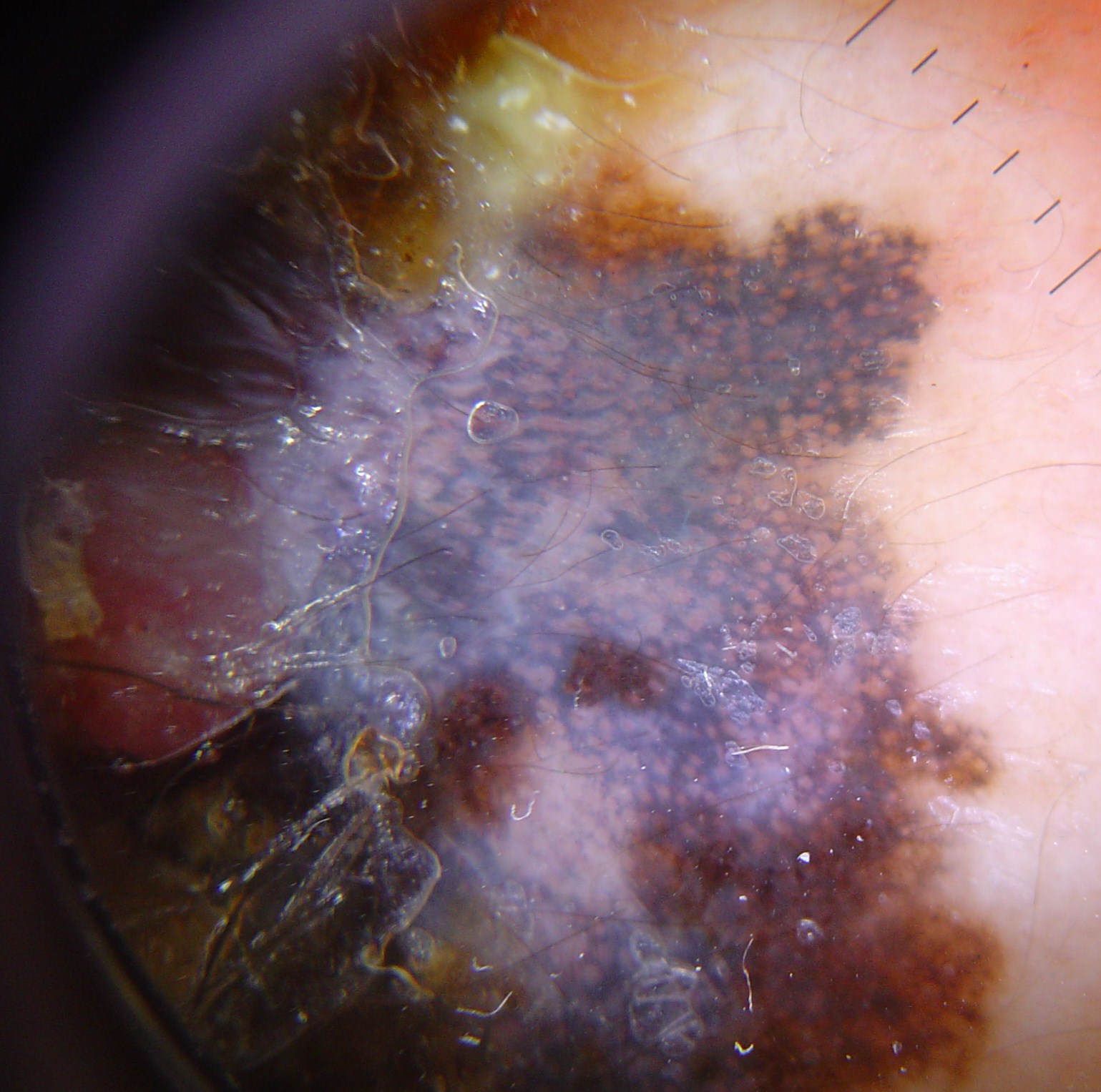Dermoscopy of a skin lesion. Biopsy-confirmed as a skin cancer — a lentigo maligna melanoma.